A dermoscopy image of a single skin lesion.
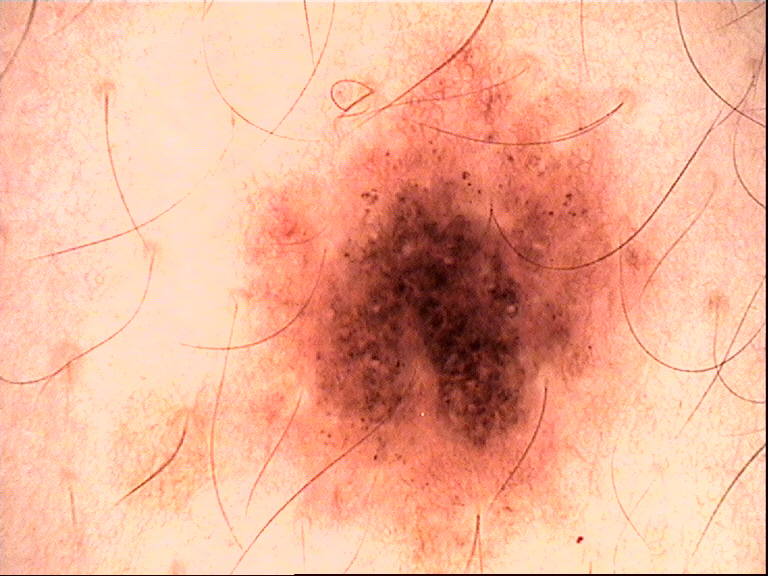Consistent with a dysplastic compound nevus.